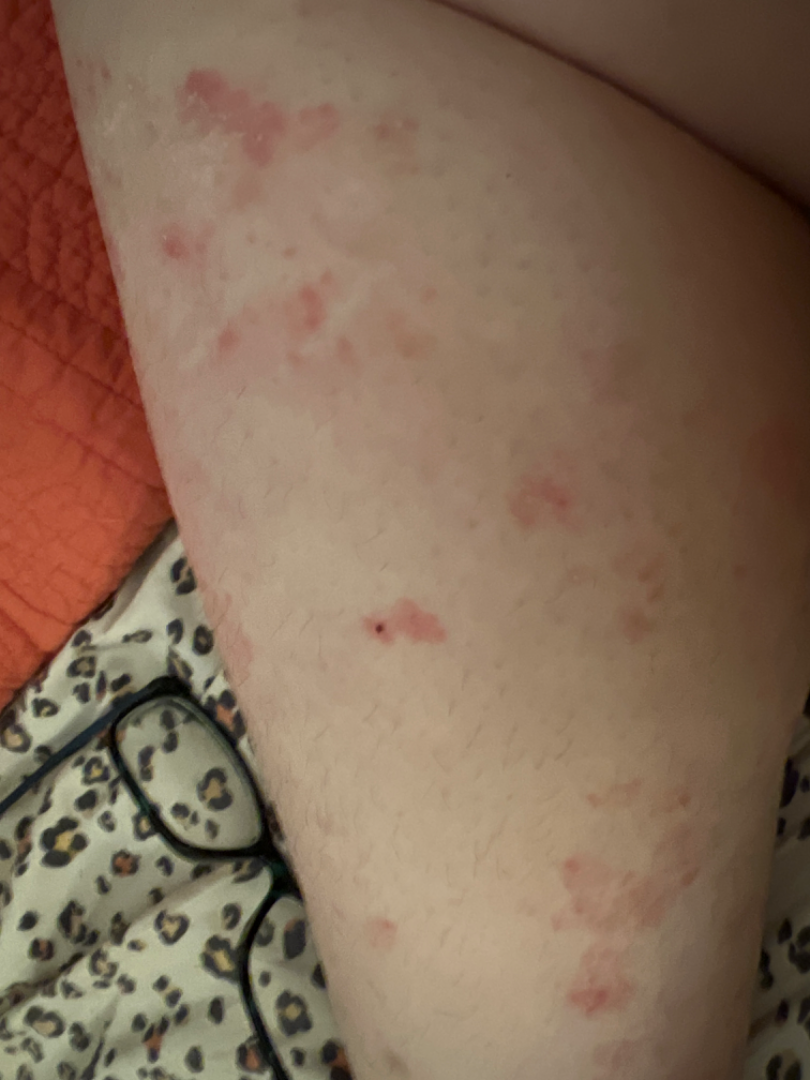{
  "differential": {
    "Tinea": 0.67,
    "Eczema": 0.33
  }
}